Located on the top or side of the foot and leg; present for three to twelve months; the subject is a male aged 40–49; the photograph is a close-up of the affected area; the patient considered this a growth or mole.
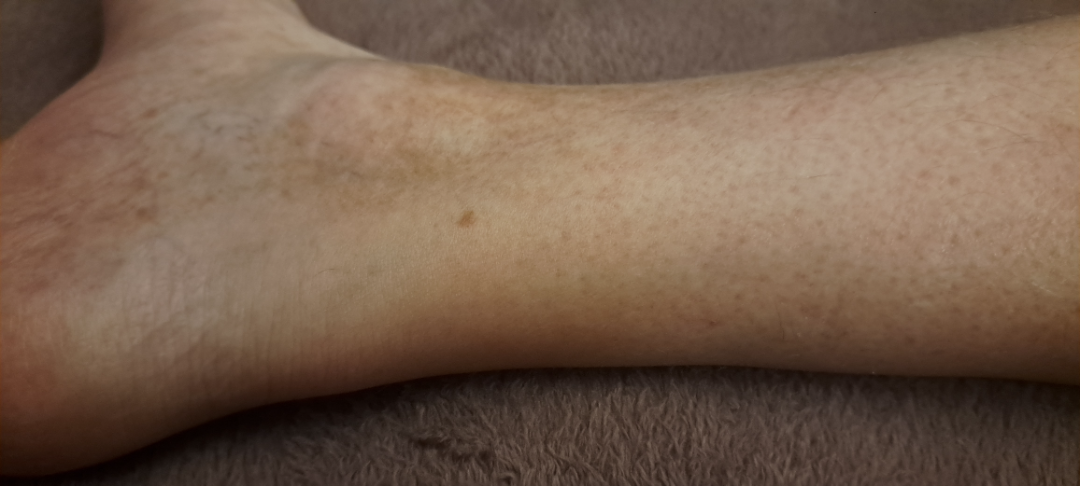differential diagnosis: Stasis Dermatitis, Pigmented purpuric eruption and Hemosiderin pigmentation of skin due to venous insufficiency were considered with similar weight.